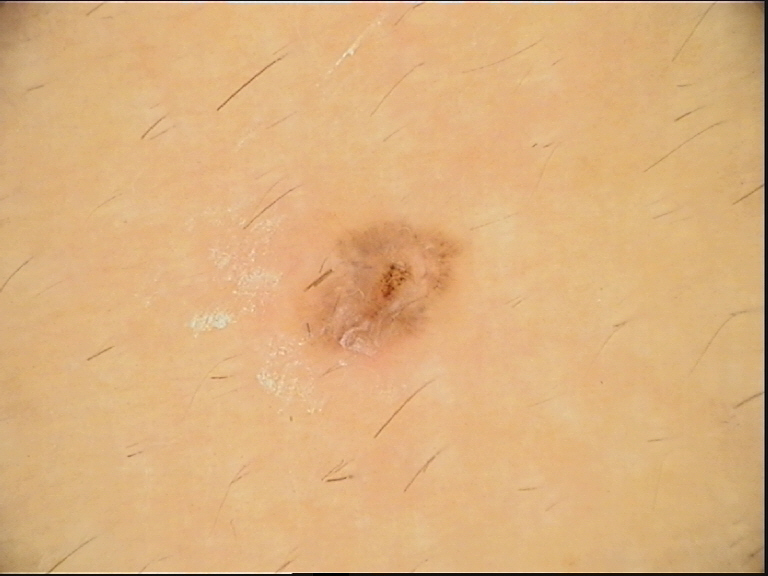A dermoscopic photograph of a skin lesion.
This is a banal lesion.
Diagnosed as a compound nevus.